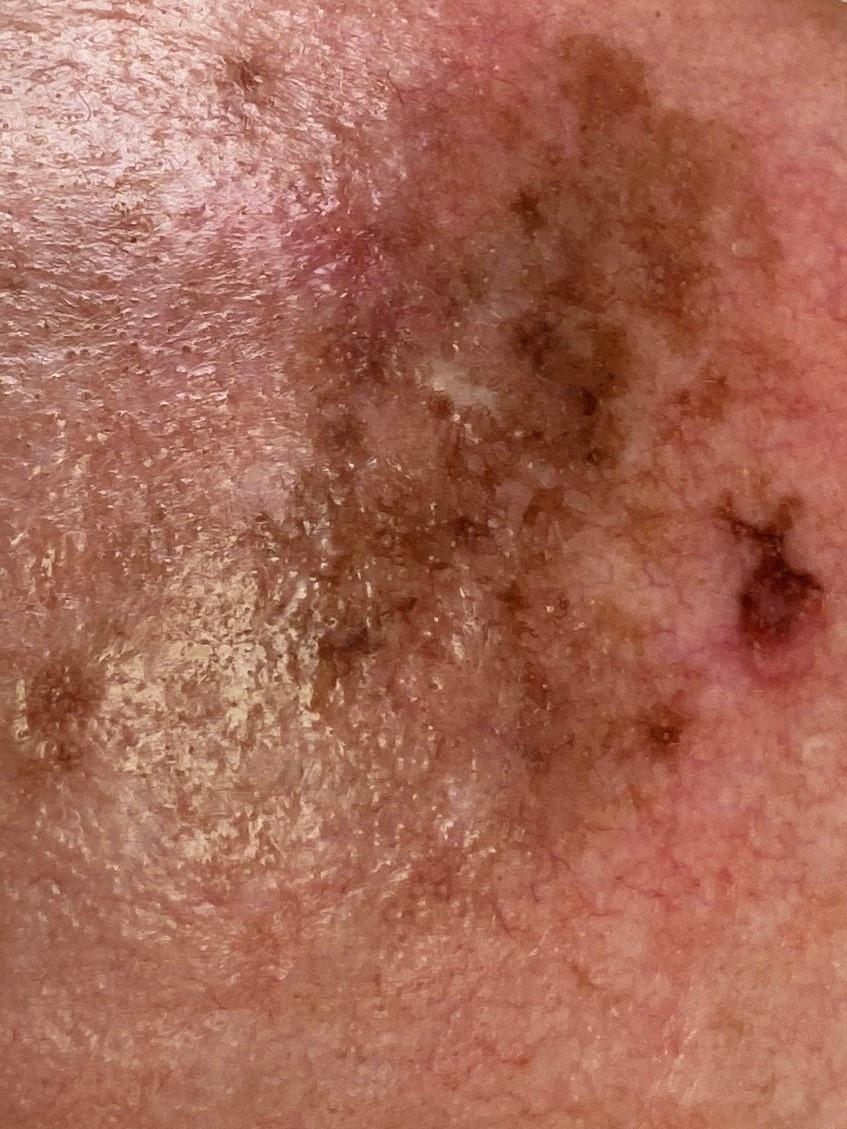Q: Any relevant melanoma history?
A: a prior melanoma
Q: What kind of image is this?
A: clinical close-up
Q: Skin phototype?
A: II
Q: Patient demographics?
A: male, in their mid- to late 80s or older
Q: What is the anatomic site?
A: the head or neck
Q: What is this lesion?
A: Melanoma (biopsy-proven)